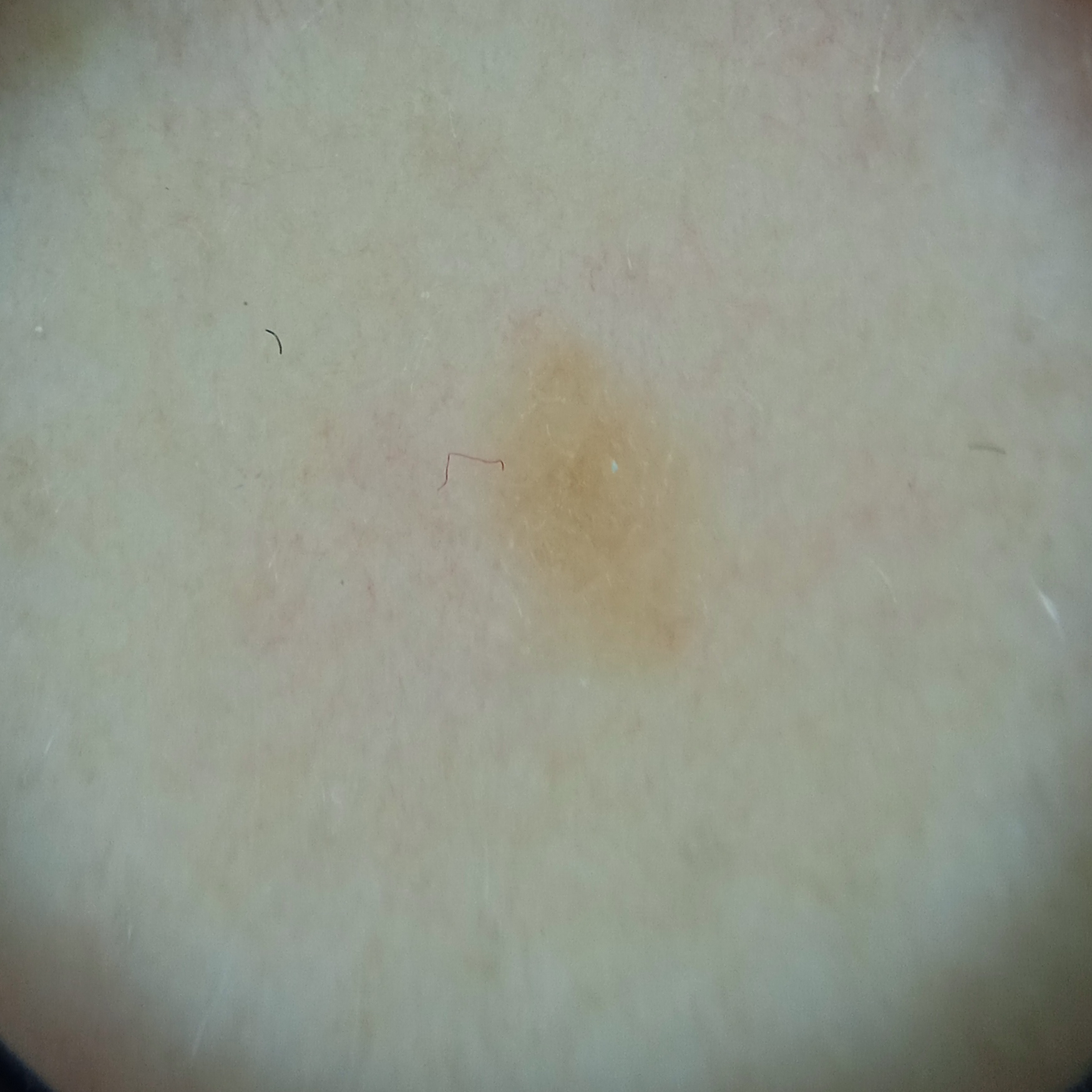Case:
– image · dermoscopic image
– referral · research study (no referral diagnosis)
– subject · female, aged 48
– lesion size · 3.8 mm
– assessment · seborrheic keratosis (dermatologist consensus)